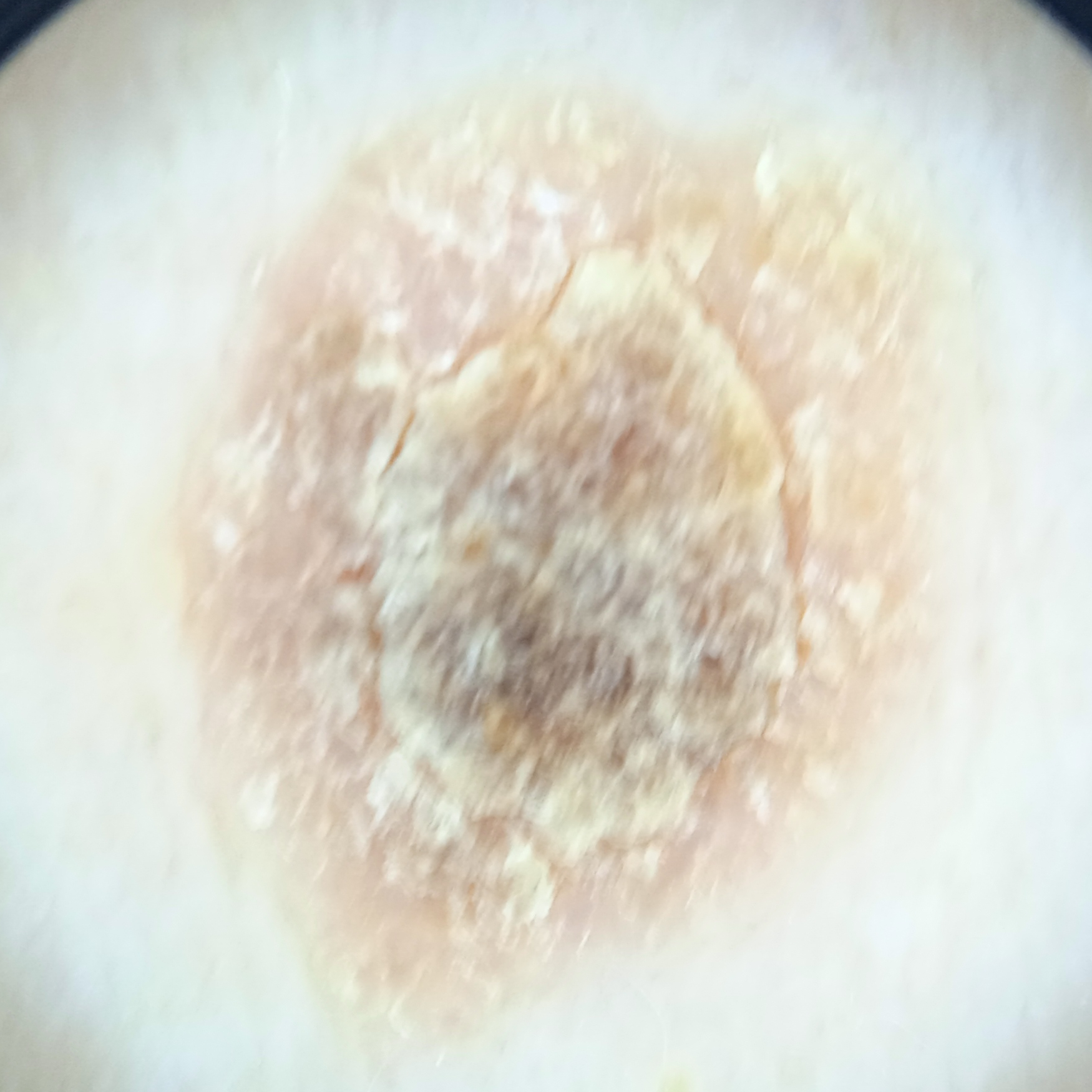assessment: seborrheic keratosis (dermatologist consensus).